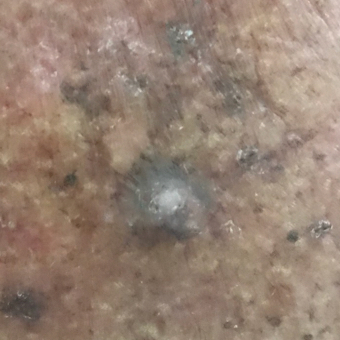subject = male, 76 years old | site = the chest | reported symptoms = itching | diagnostic label = squamous cell carcinoma (biopsy-proven).